The affected area is the back of the hand; the photograph is a close-up of the affected area — 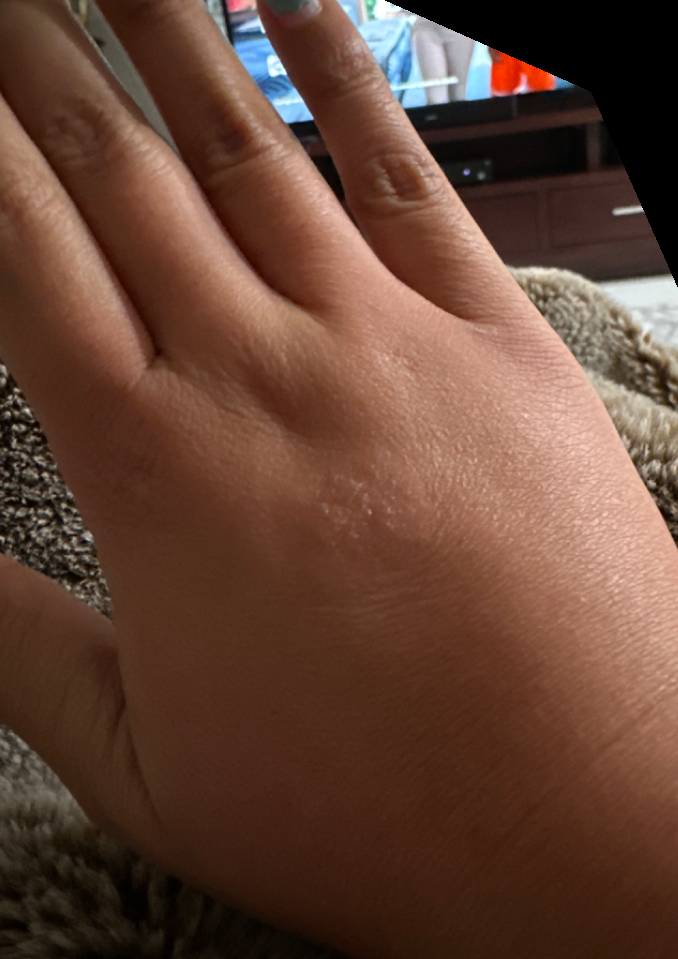The image was not sufficient for the reviewer to characterize the skin condition.
The lesion is associated with itching.
The lesion is described as raised or bumpy.
The condition has been present for about one day.
Self-categorized by the patient as a rash.